The photograph was taken at a distance.
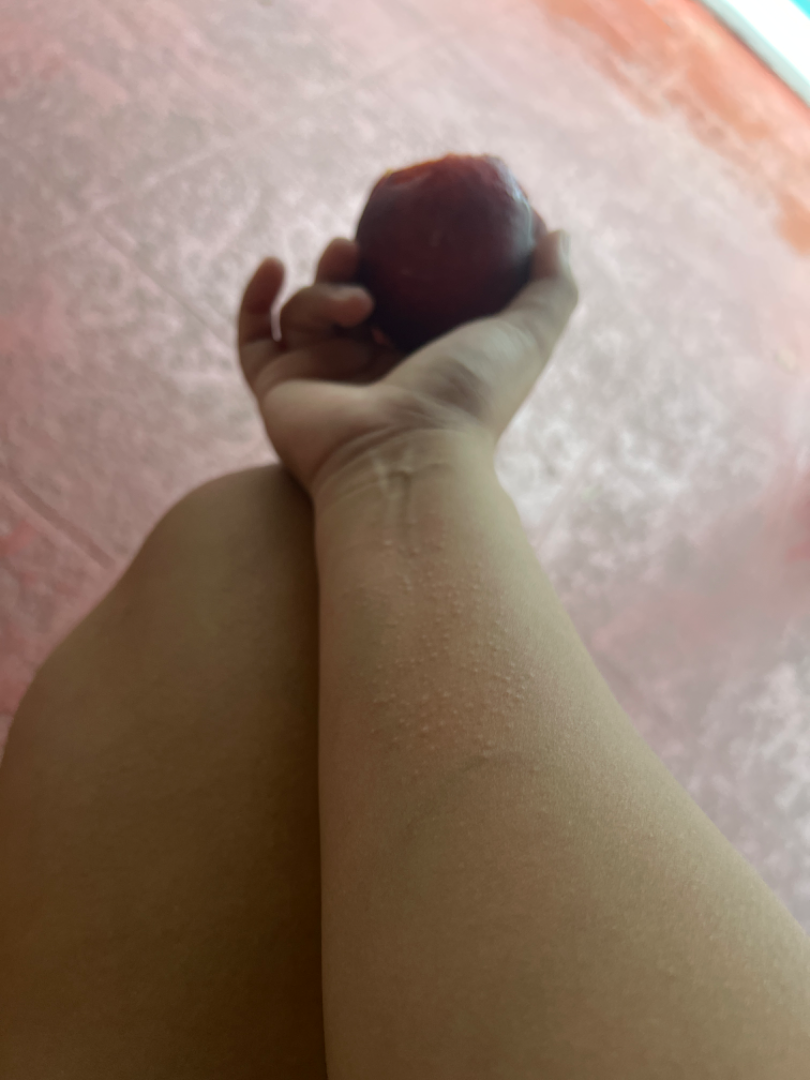The reviewing dermatologist's impression was: Lichen nitidus (most likely); Miliaria (possible); Allergic Contact Dermatitis (possible).